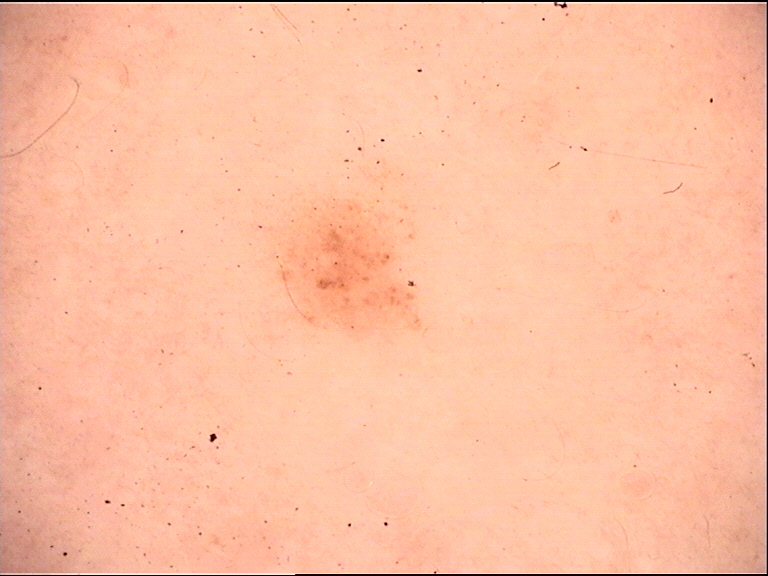Q: What was the diagnostic impression?
A: dysplastic junctional nevus (expert consensus)